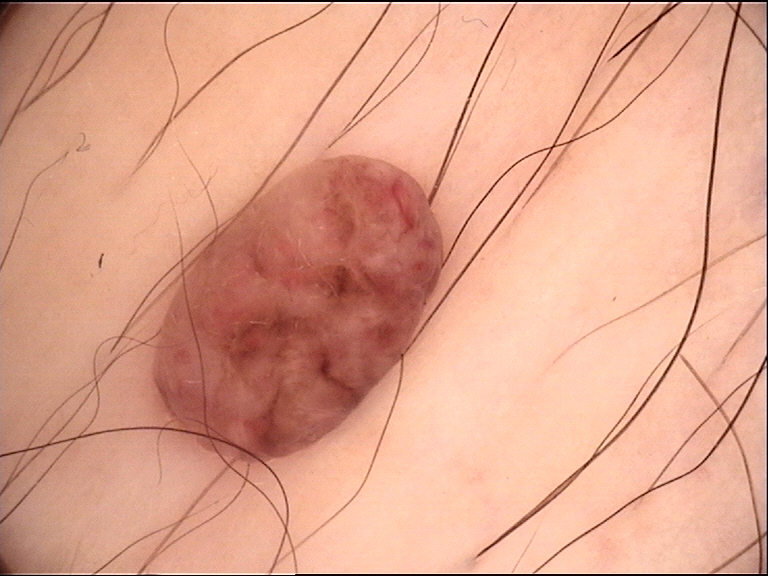Q: What kind of image is this?
A: dermatoscopy
Q: What is the diagnosis?
A: dermal nevus (expert consensus)